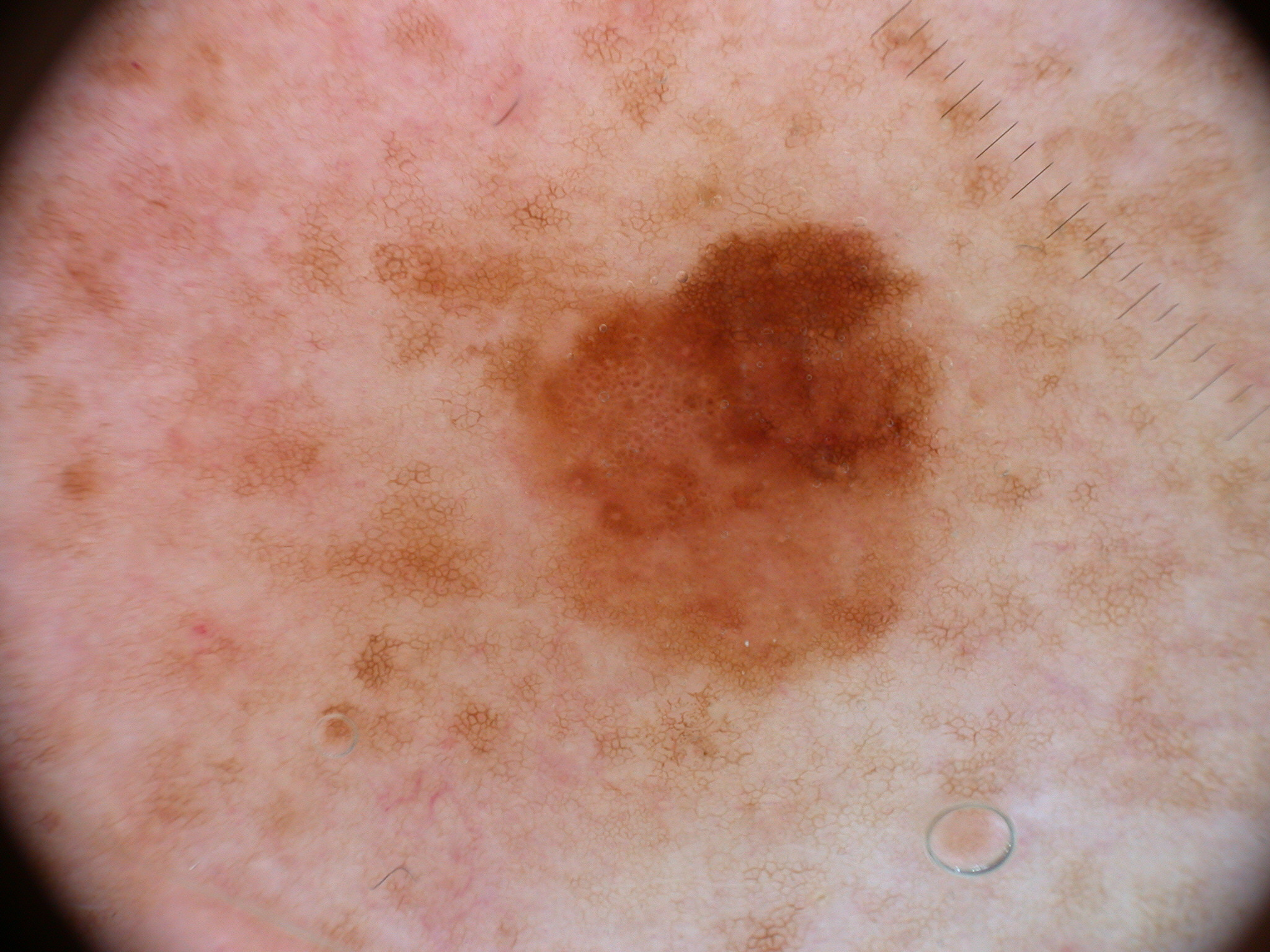Q: What is the imaging modality?
A: dermoscopic image
Q: What does dermoscopy show?
A: negative network and pigment network; absent: globules, streaks, and milia-like cysts
Q: How much of the field does the lesion occupy?
A: ~14% of the field
Q: Where is the lesion located?
A: x1=498 y1=216 x2=960 y2=699
Q: What is this lesion?
A: a melanocytic nevus, a benign lesion